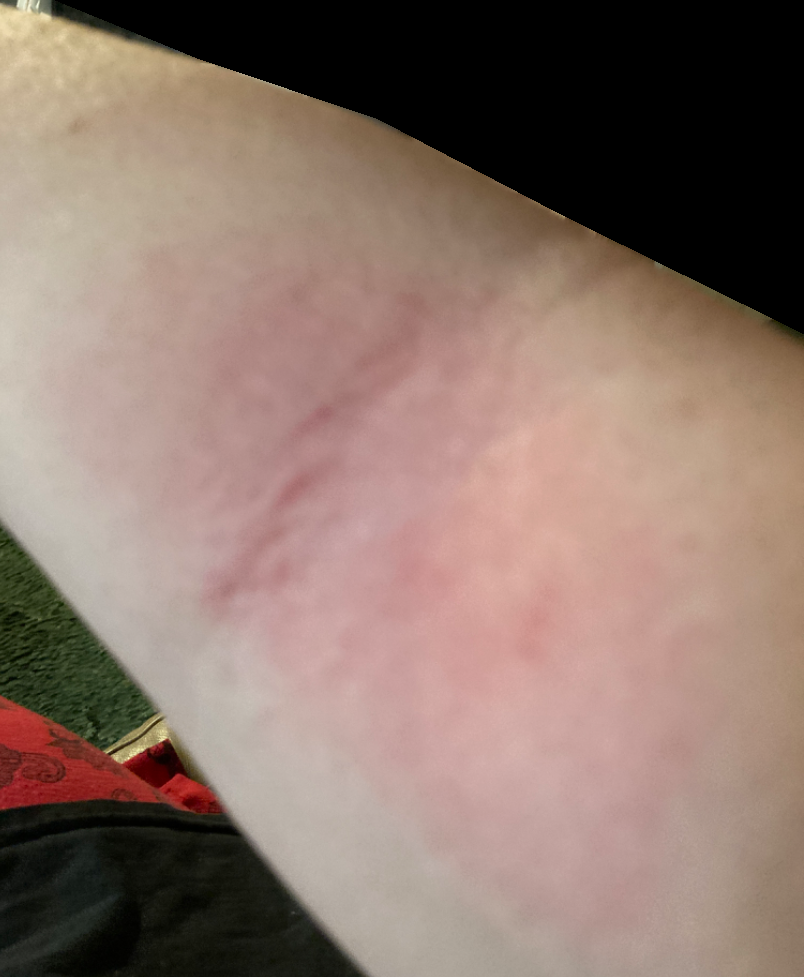Q: Reported symptoms?
A: itching
Q: What is the framing?
A: close-up
Q: How long has this been present?
A: less than one week
Q: Patient's own categorization?
A: a rash
Q: What is the patient's skin tone?
A: lay reviewers estimated 2 on the MST
Q: Anatomic location?
A: arm, back of the hand and leg
Q: Texture?
A: raised or bumpy
Q: What is the differential diagnosis?
A: most consistent with Eczema; also consider Allergic Contact Dermatitis